The photograph was taken at a distance. The lesion involves the back of the hand. Male contributor, age 18–29:
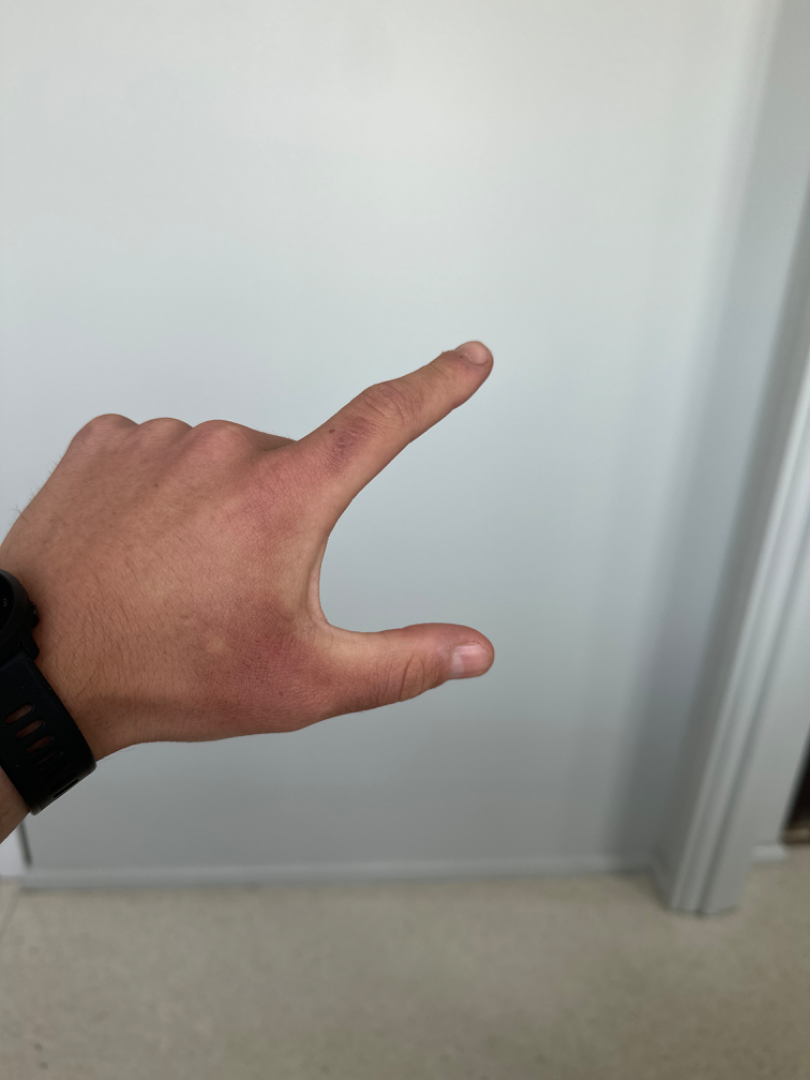<dermatology_case>
  <assessment>could not be assessed</assessment>
  <duration>one to four weeks</duration>
  <texture>rough or flaky</texture>
  <patient_category>a rash</patient_category>
  <symptoms>darkening</symptoms>
</dermatology_case>